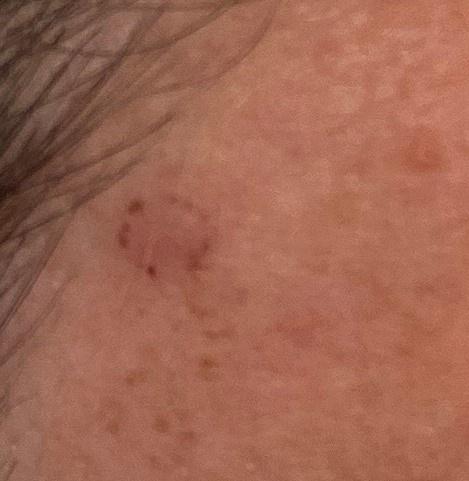Findings:
• subject · female, aged 43-47
• imaging · clinical overview photograph
• FST · II
• body site · the head or neck
• diagnosis · Basal cell carcinoma (biopsy-proven)